The photo was captured at a distance.
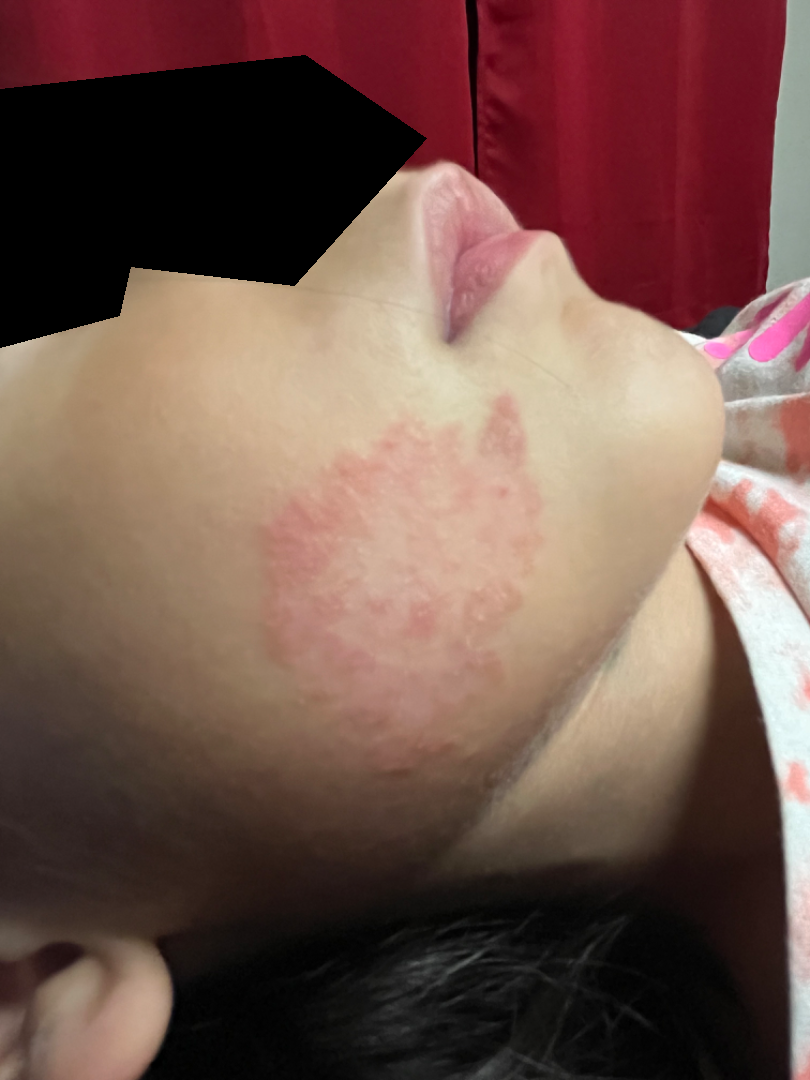Findings: The reviewing dermatologist's impression was: the favored diagnosis is Hemangioma; with consideration of Granuloma faciale.